The photograph is a close-up of the affected area.
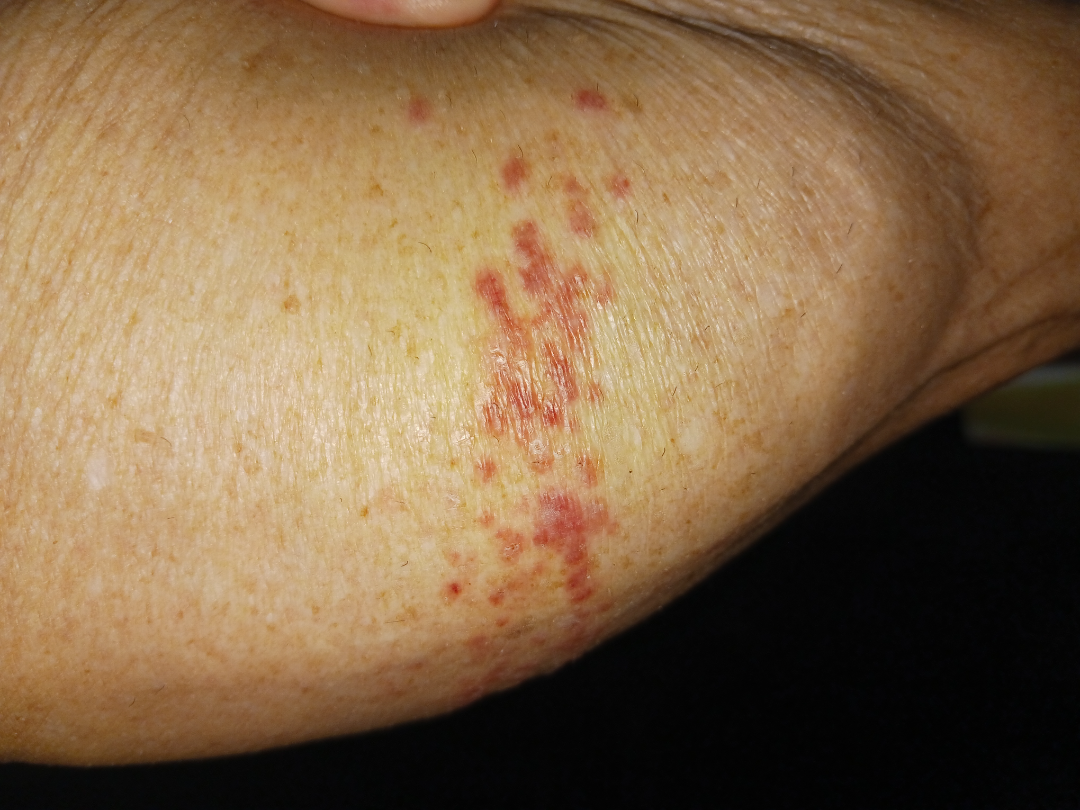Impression:
Ecchymoses (leading); Eczema (possible).